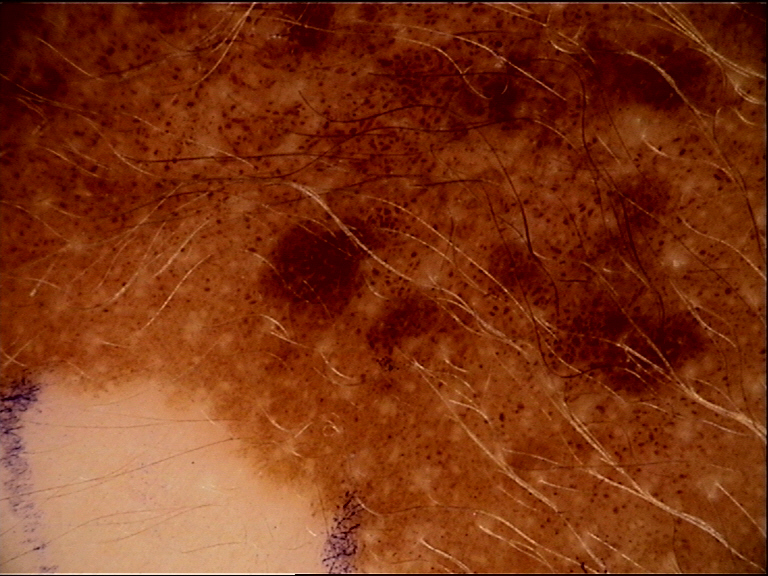Q: What is the lesion category?
A: banal
Q: What was the diagnostic impression?
A: congenital junctional nevus (expert consensus)